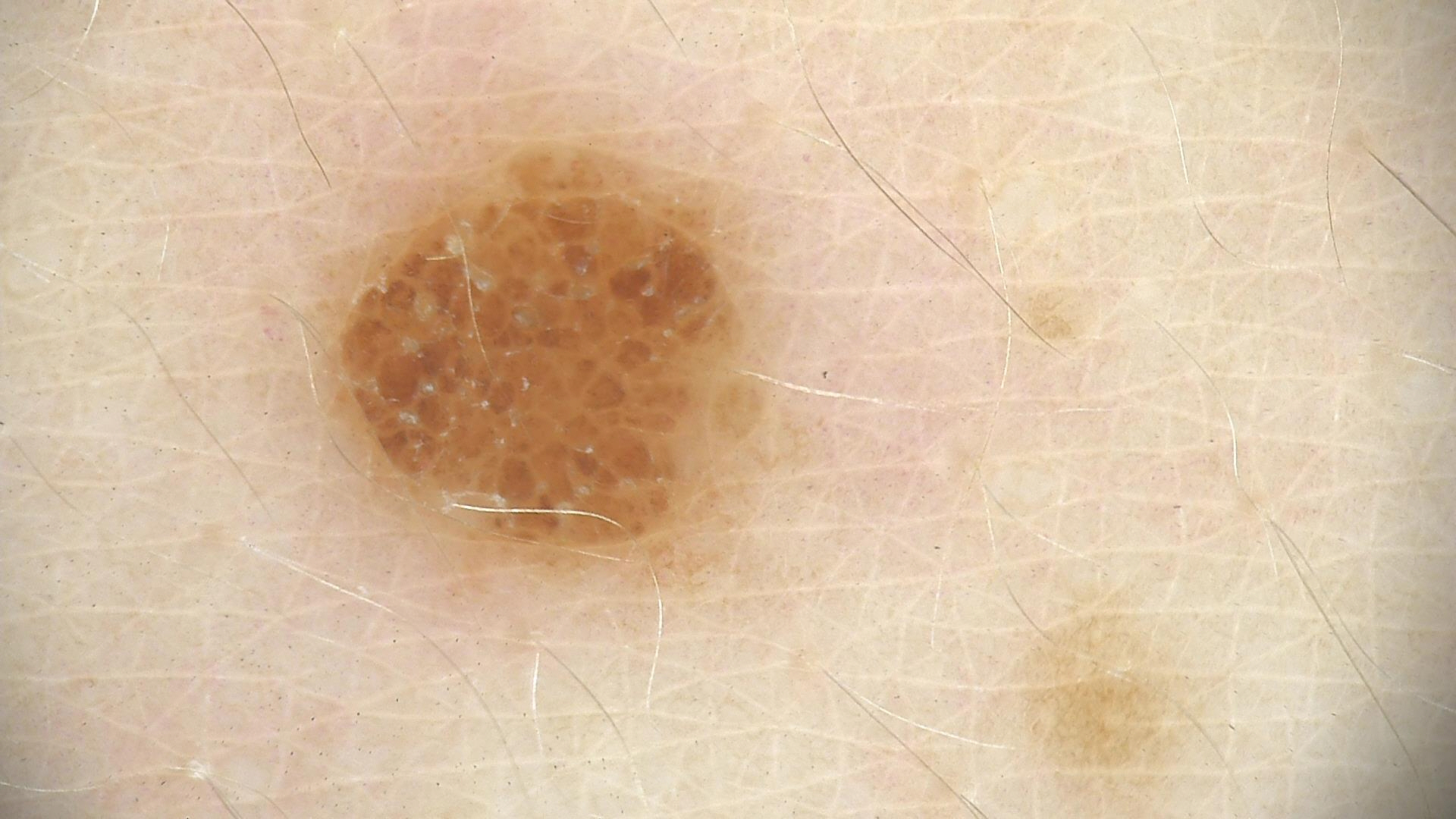Diagnosed as a banal lesion — a compound nevus.